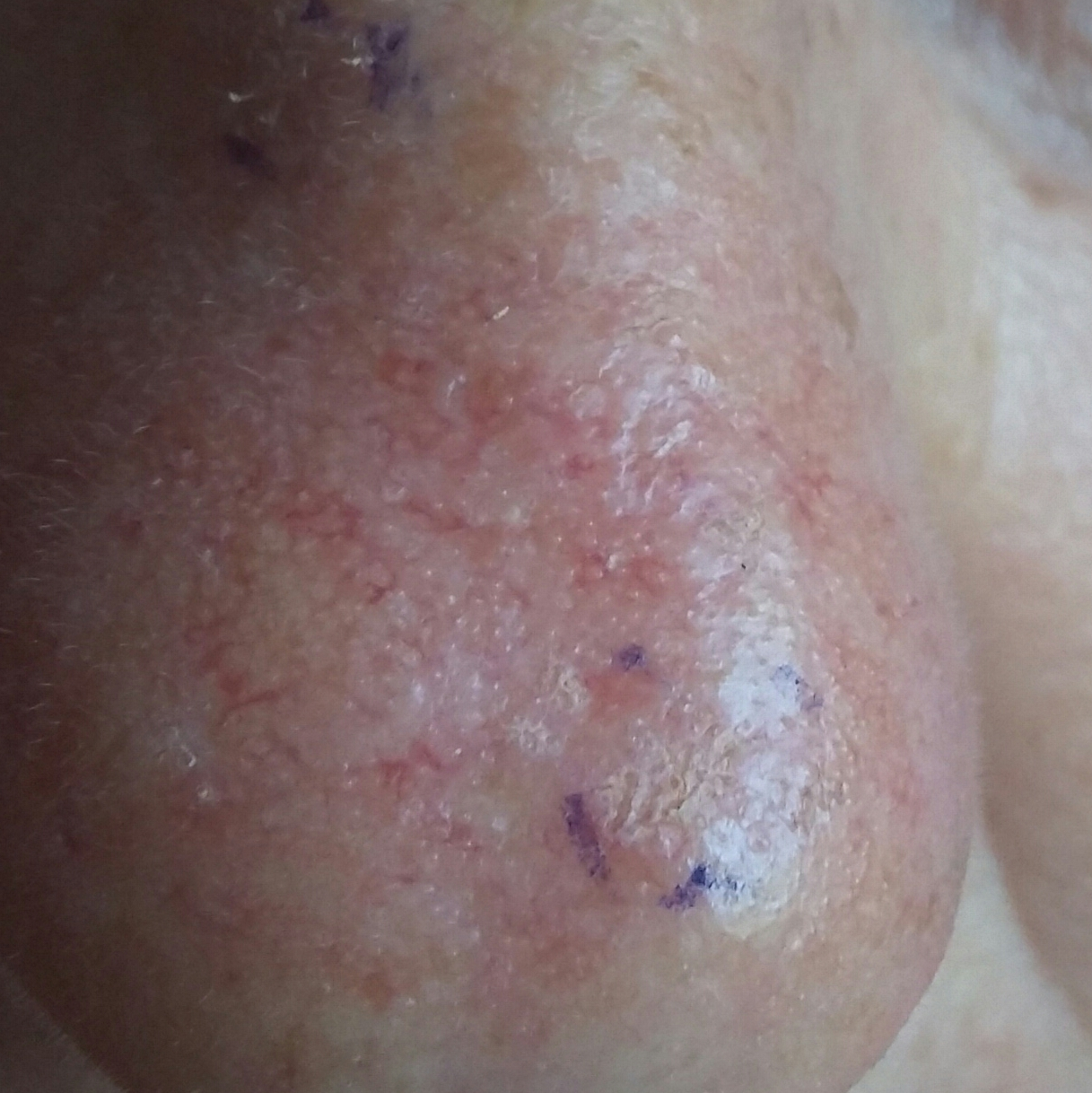A clinical photograph of a skin lesion.
A patient in their 50s.
The lesion is on the nose.
By the patient's account, the lesion has grown and itches, but does not hurt.
Diagnosed by dermatologist consensus as an actinic keratosis.